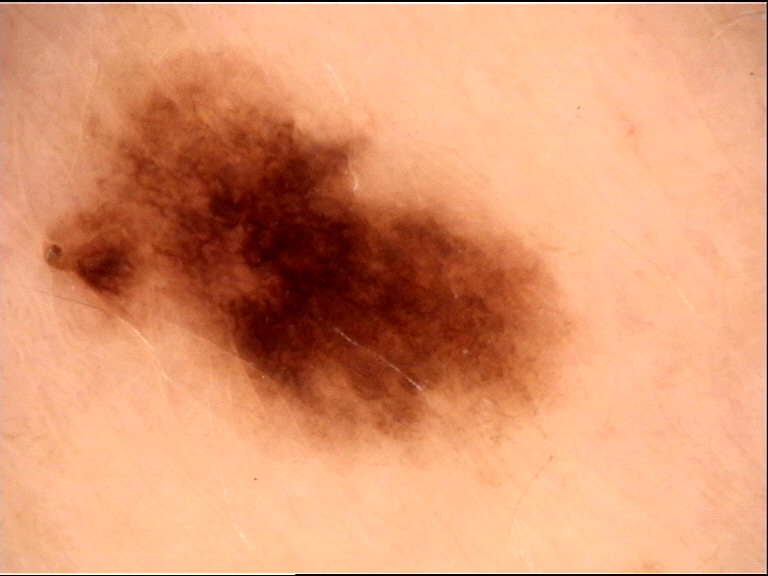Dermoscopy of a skin lesion. The diagnosis was a dysplastic junctional nevus.